This image was taken at a distance.
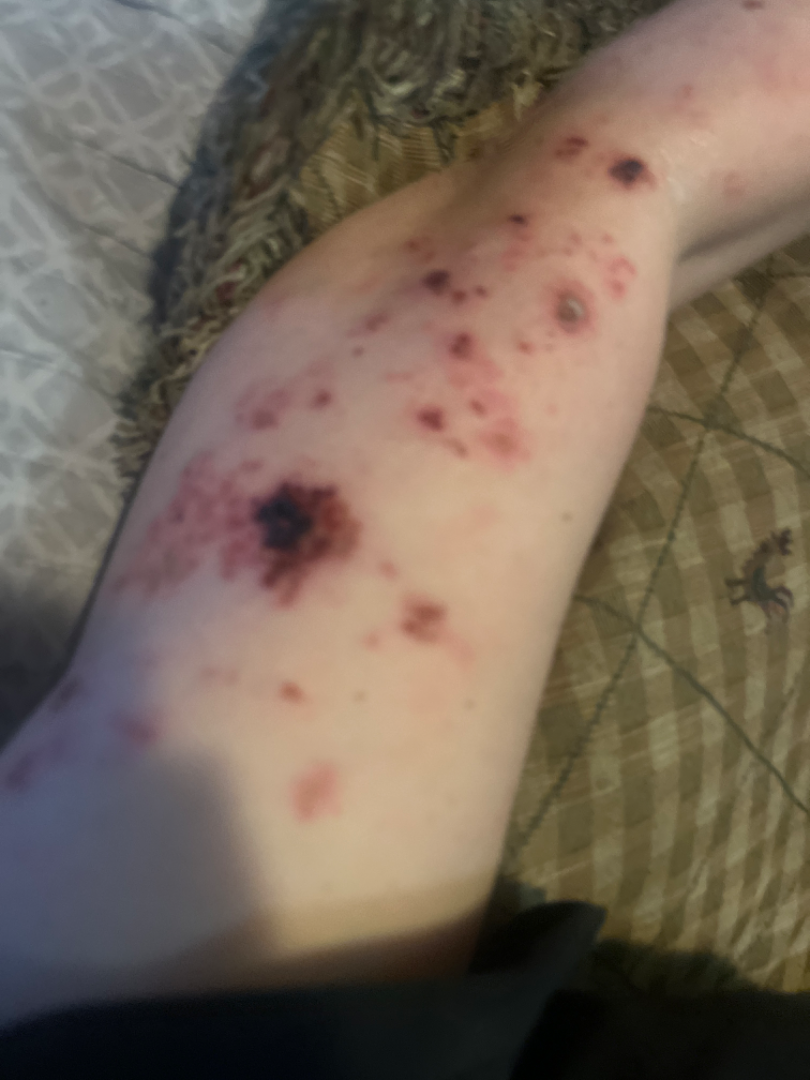The differential includes Infected eczema, Herpes Zoster and Leukocytoclastic Vasculitis, with no clear leading consideration.